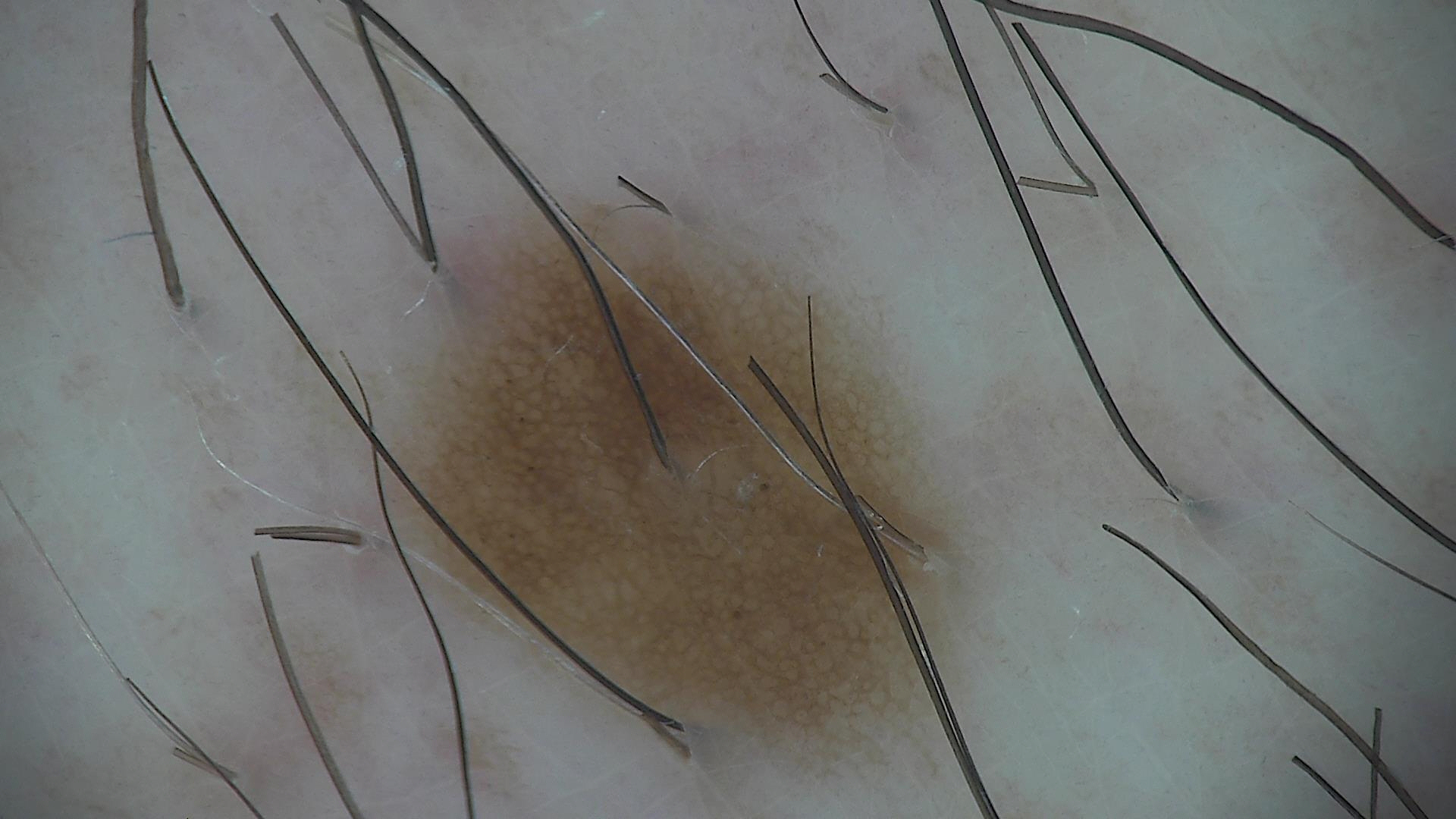Findings:
– diagnosis — dysplastic junctional nevus (expert consensus)